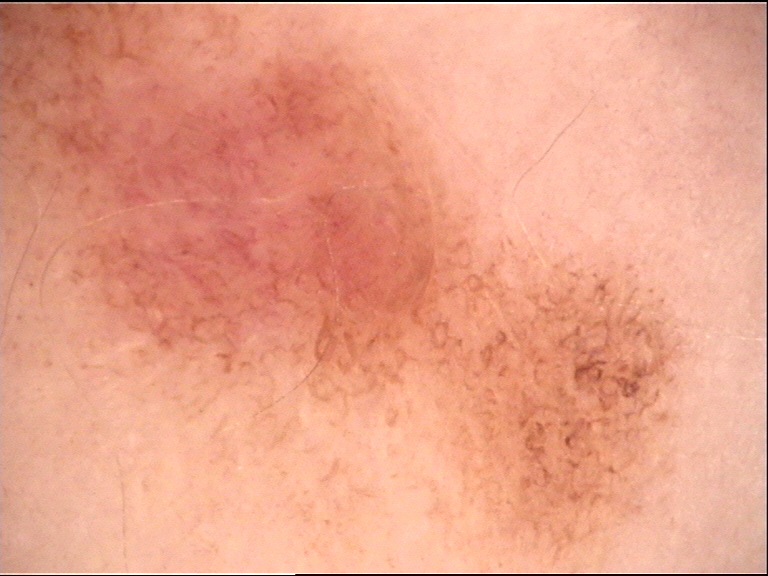Labeled as a dysplastic junctional nevus.